A dermoscopic image of a skin lesion.
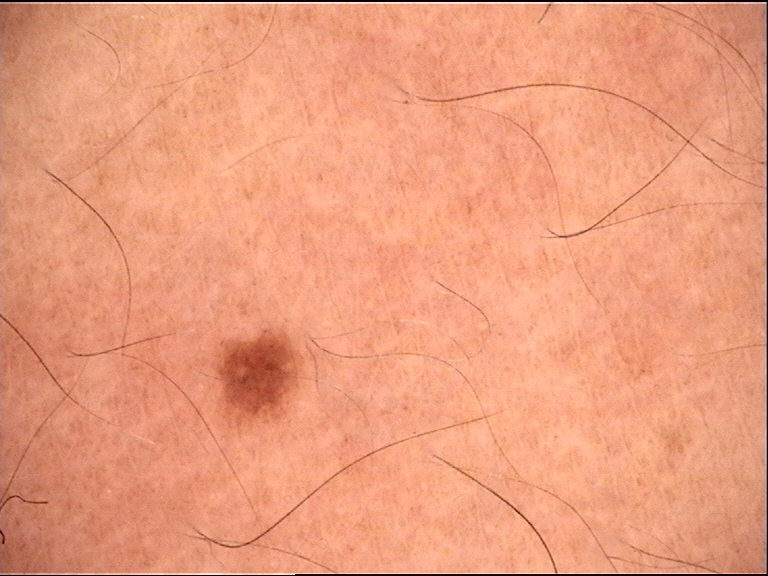Findings:
- label — dysplastic junctional nevus (expert consensus)